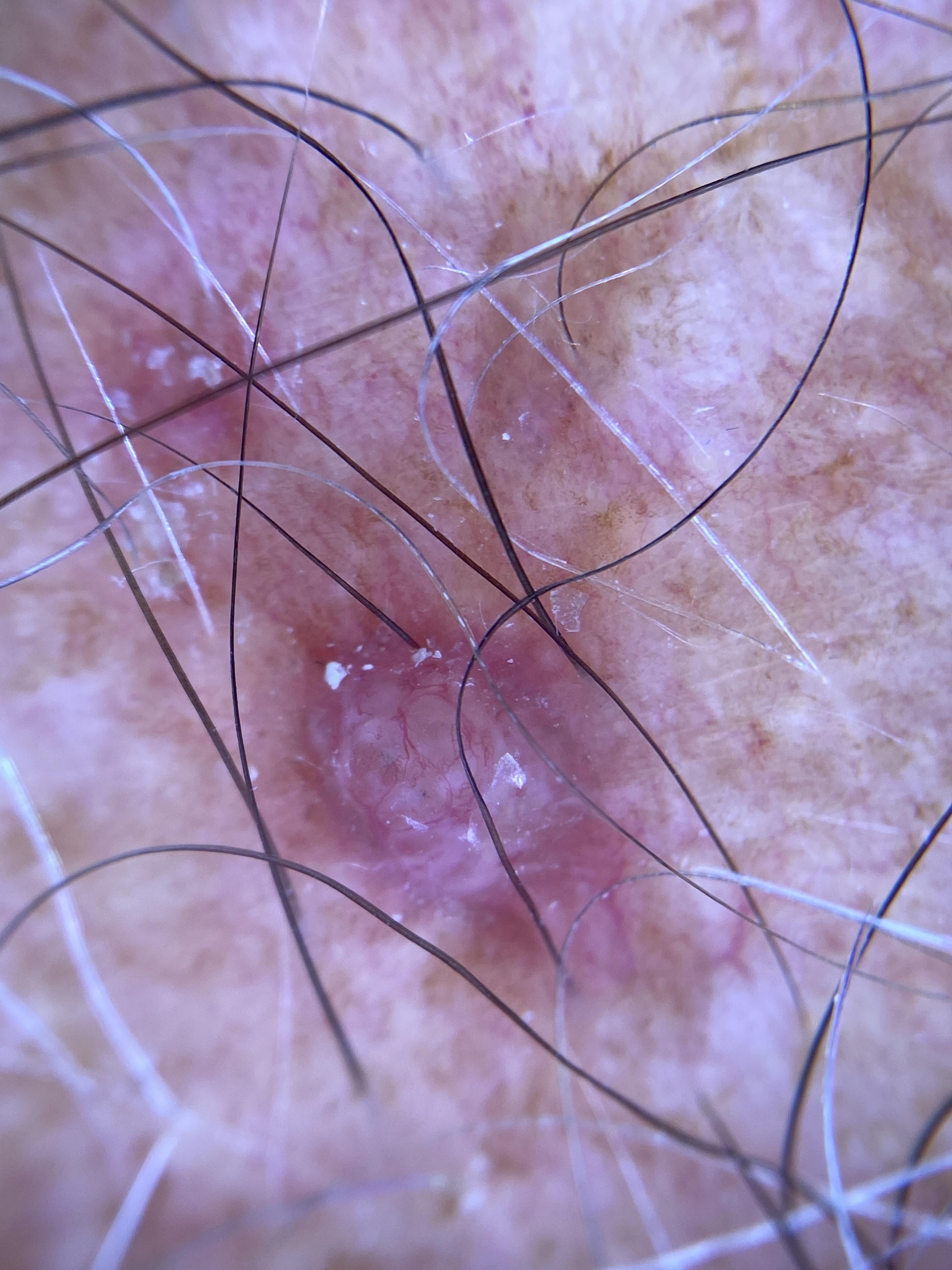| key | value |
|---|---|
| subject | male, roughly 80 years of age |
| image type | contact-polarized dermoscopy |
| location | the anterior trunk |
| pathology | Basal cell carcinoma (biopsy-proven) |